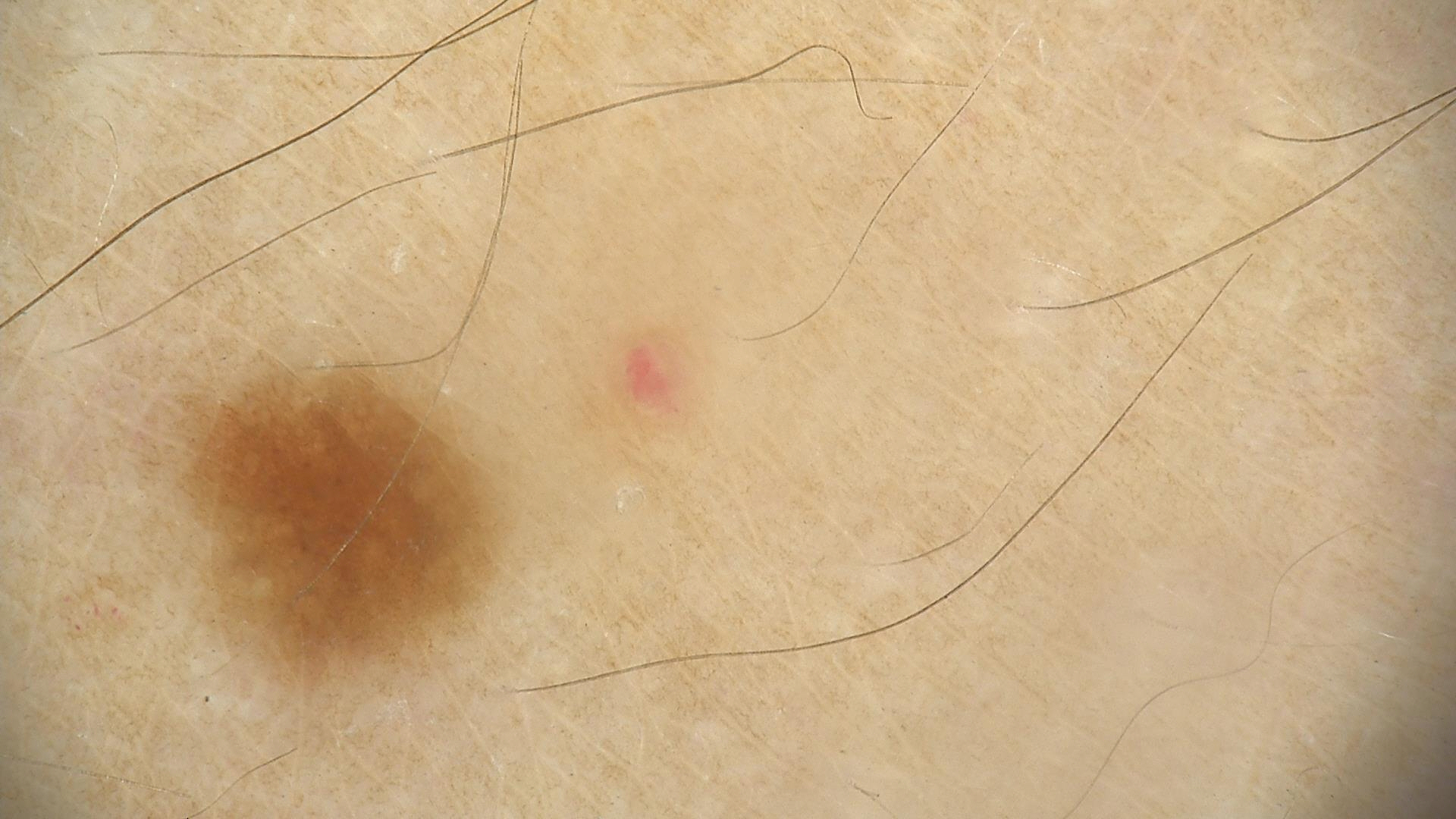Conclusion: Consistent with a dysplastic junctional nevus.